The photograph is a close-up of the affected area. Located on the arm: 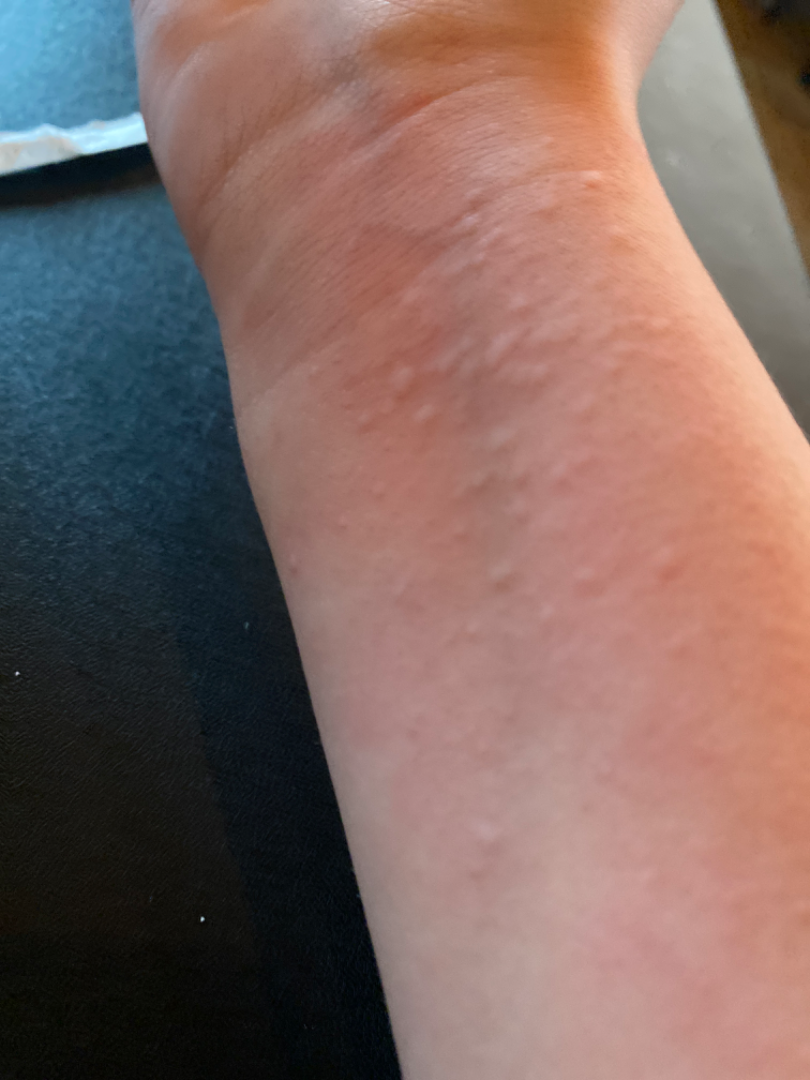Clinical context:
Texture is reported as raised or bumpy. Symptoms reported: itching.
Assessment:
In keeping with Urticaria.